A dermoscopy image of a single skin lesion: 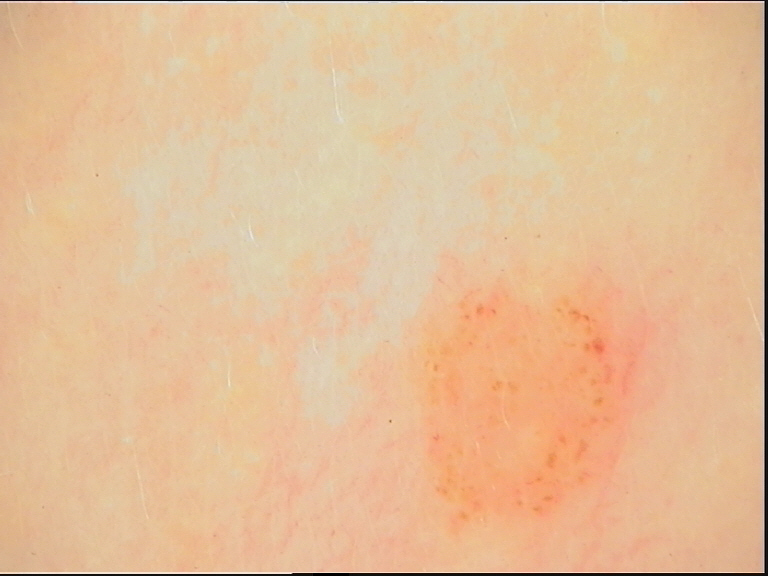<lesion>
<diagnosis>
<name>dysplastic compound nevus</name>
<code>cd</code>
<malignancy>benign</malignancy>
<super_class>melanocytic</super_class>
<confirmation>expert consensus</confirmation>
</diagnosis>
</lesion>